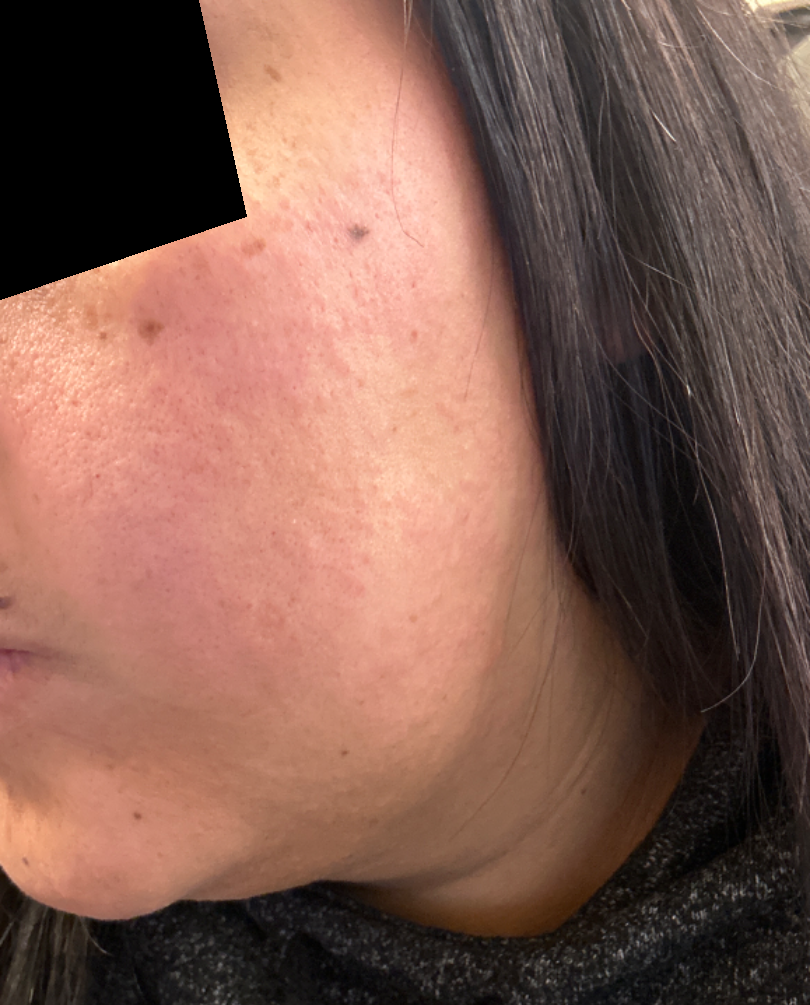Case summary:
• onset — less than one week
• self-categorized as — a rash
• body site — head or neck
• shot type — at an angle
• lesion symptoms — burning and itching
• dermatologist impression — single-reviewer assessment: favoring Rosacea; also consider Irritant Contact Dermatitis